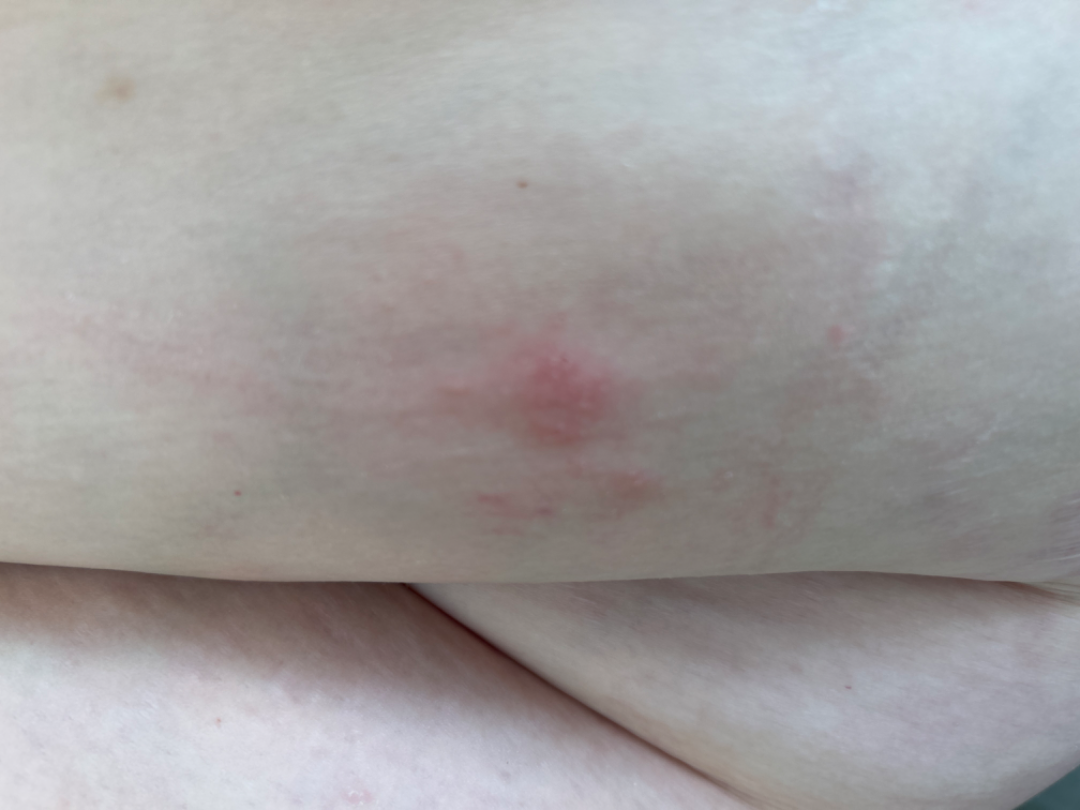<dermatology_case>
  <differential>
    <tied_lead>Herpes Zoster, Herpes Simplex</tied_lead>
    <unlikely>Allergic Contact Dermatitis</unlikely>
  </differential>
</dermatology_case>